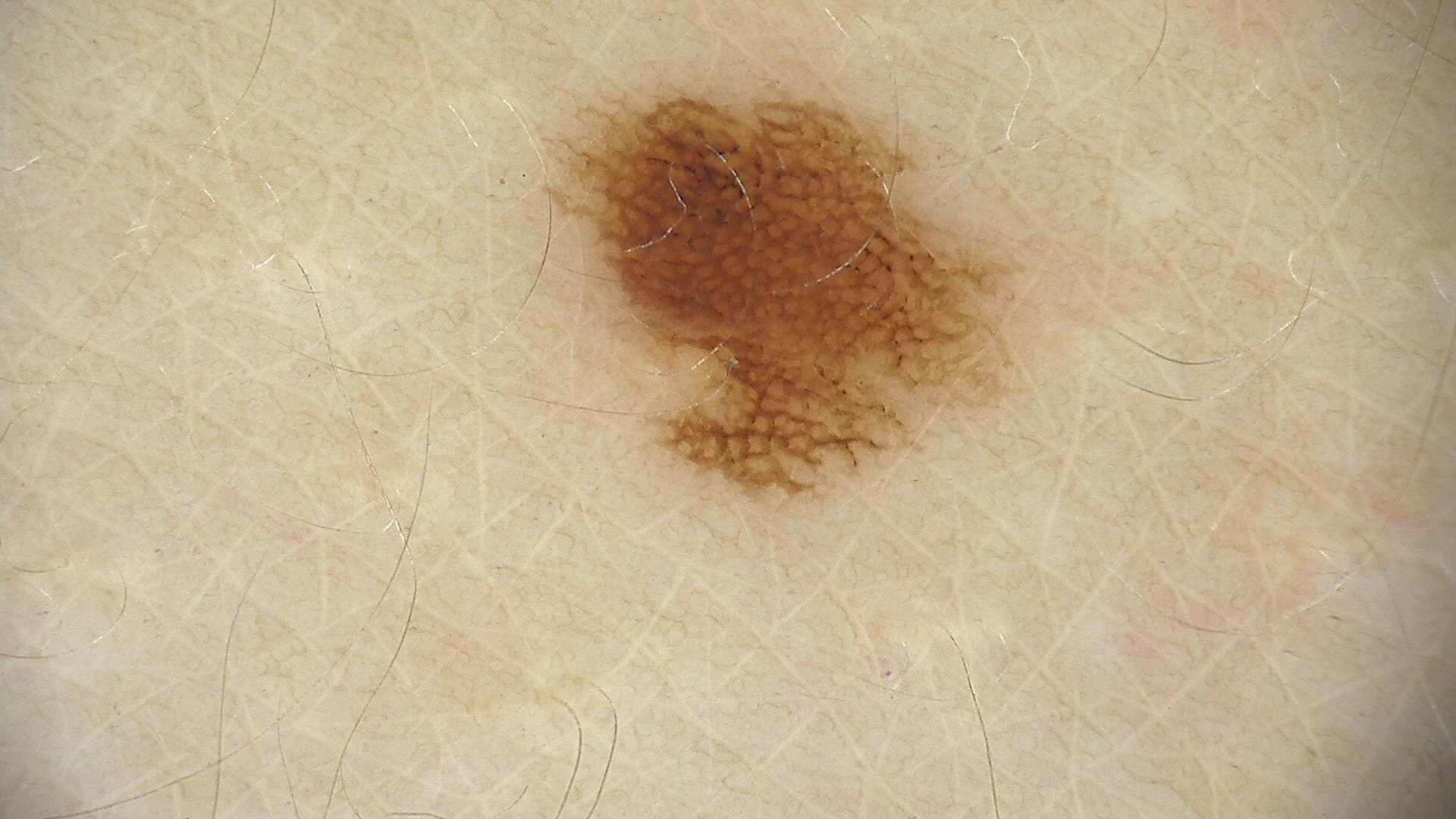Q: What is the diagnosis?
A: dysplastic junctional nevus (expert consensus)